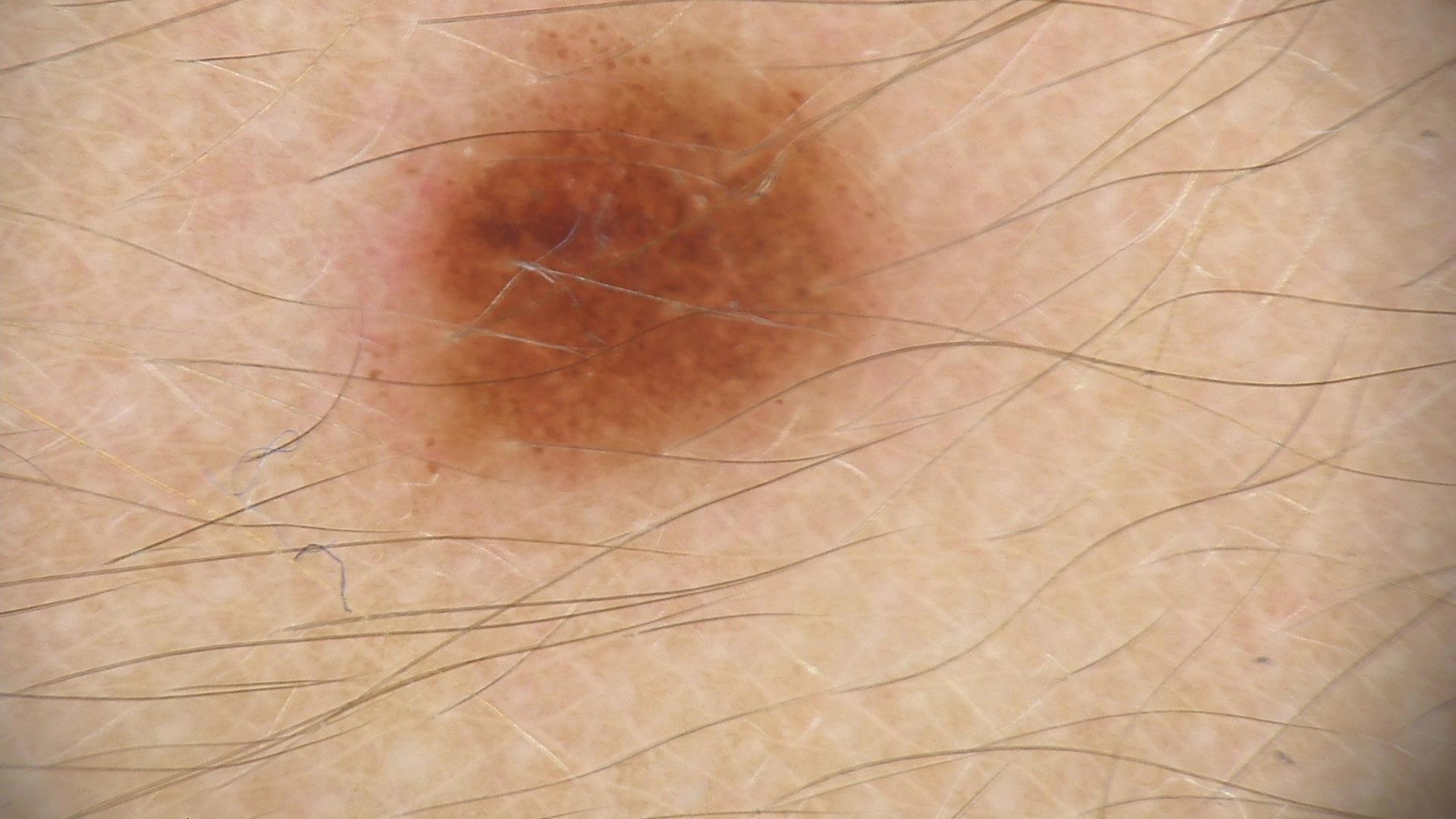imaging: dermoscopy
diagnosis: dysplastic junctional nevus (expert consensus)